A dermoscopy image of a single skin lesion: 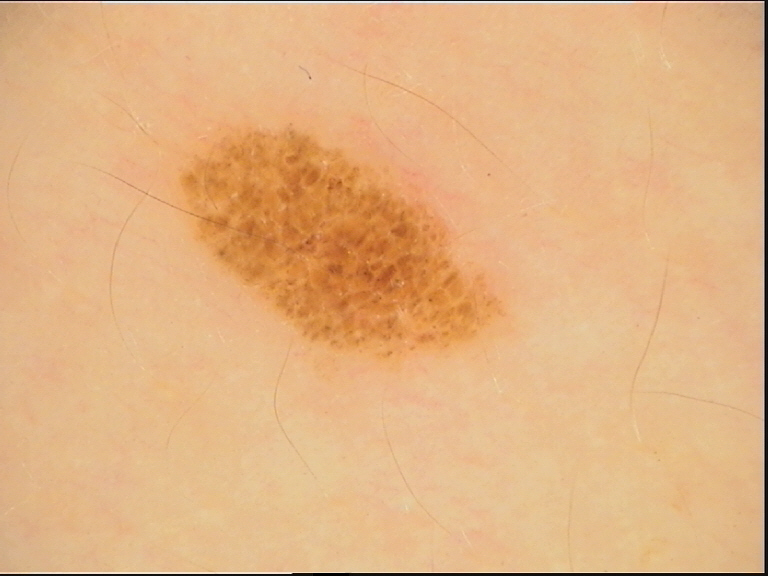The diagnostic label was a dysplastic compound nevus.